A female subject; a dermoscopic image of a skin lesion:
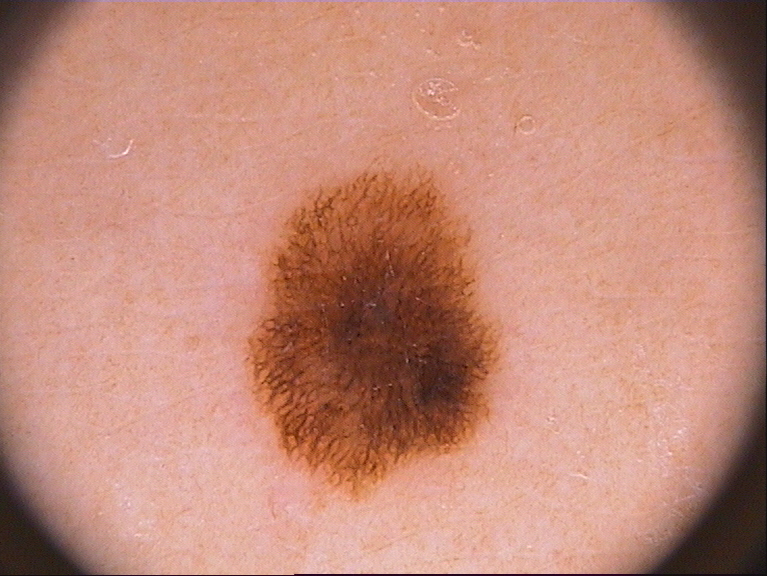A moderately sized lesion. The lesion is located at box(239, 157, 509, 500). Dermoscopically, the lesion shows pigment network; no streaks, negative network, globules, or milia-like cysts. Diagnosed as a melanocytic nevus.